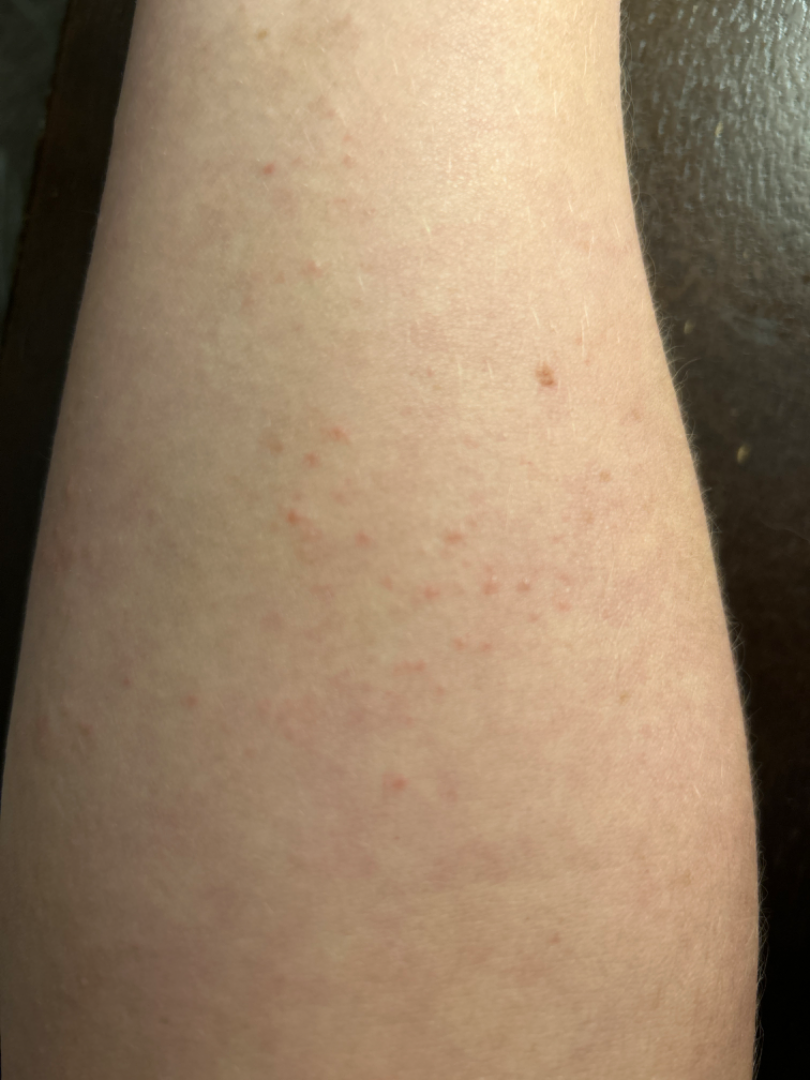Symptoms reported: itching. The photograph is a close-up of the affected area. The arm is involved. The patient reports the lesion is raised or bumpy. Present for less than one week. On remote review of the image: most likely Keratosis pilaris; with consideration of Irritant Contact Dermatitis.